Dermoscopy of a skin lesion: 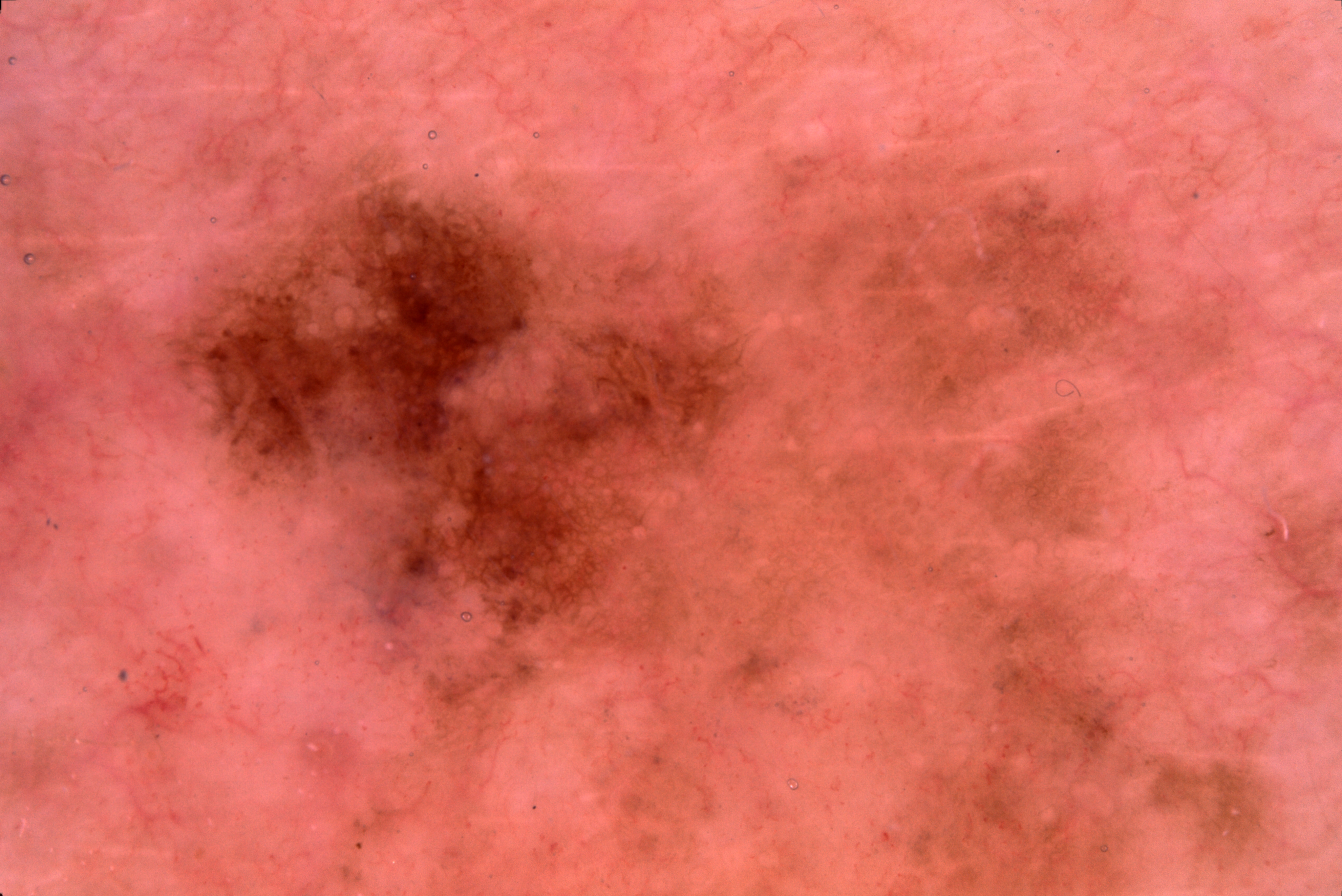extent = ~17% of the field; lesion location = (162, 135, 769, 769); dermoscopic pattern = pigment network; impression = a melanoma.